This is a dermoscopic photograph of a skin lesion — 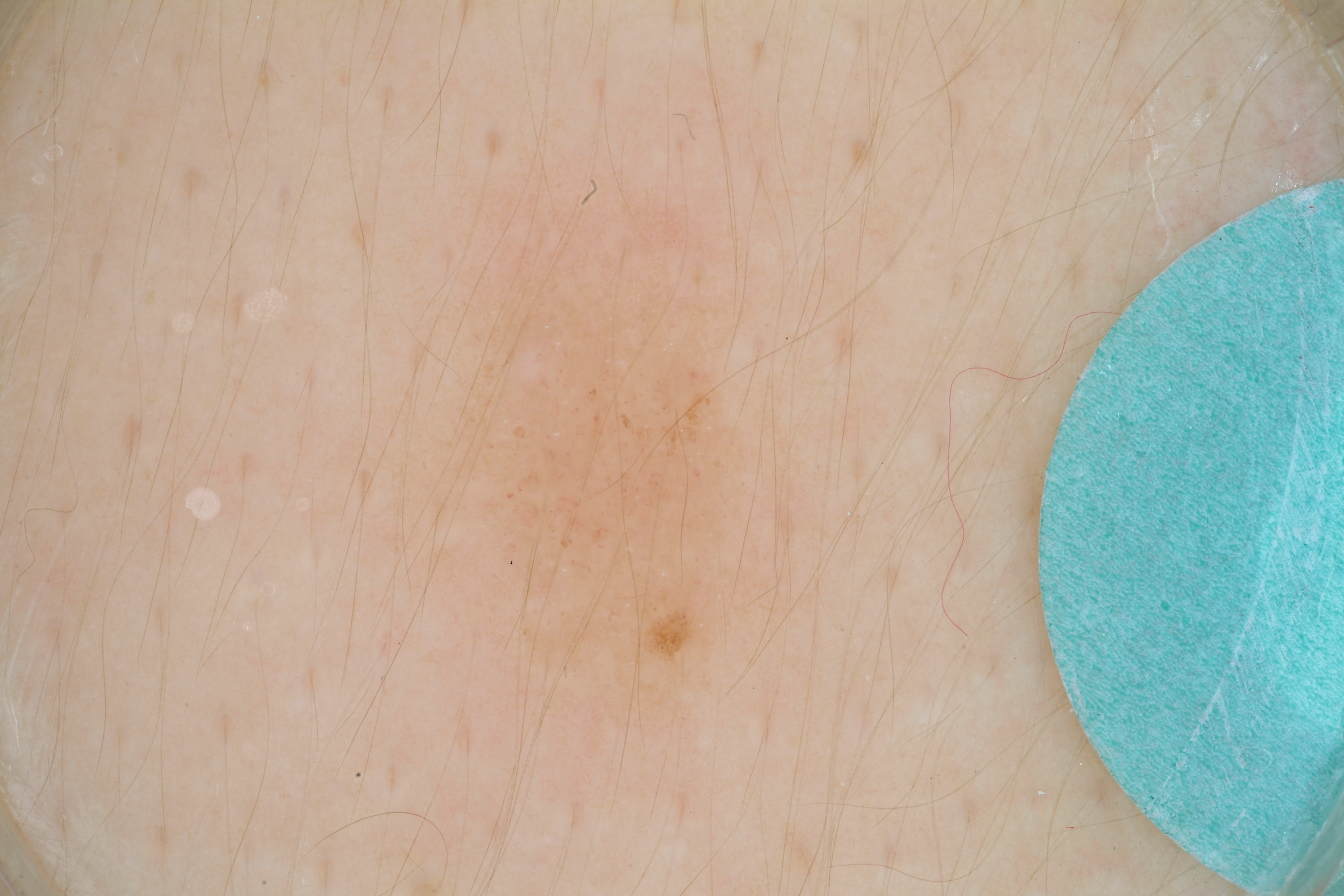The dermoscopic pattern shows neither streaks nor globules. As (left, top, right, bottom), the lesion occupies the region [447,229,751,717]. Consistent with a benign skin lesion.